A dermoscopy image of a single skin lesion.
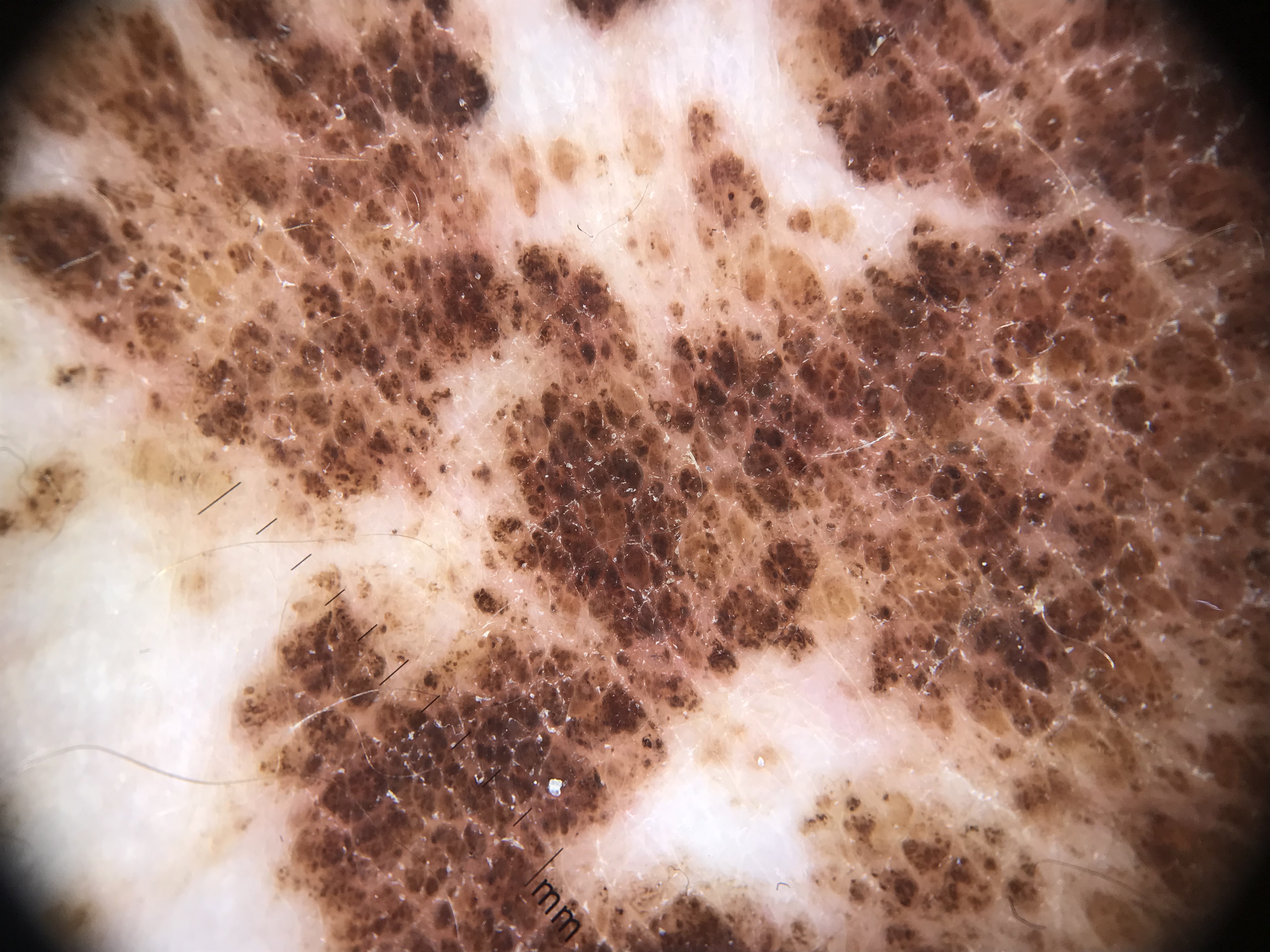  diagnosis:
    name: congenital junctional nevus
    code: cjb
    malignancy: benign
    super_class: melanocytic
    confirmation: expert consensus